A female patient aged 48 to 52. A dermoscopic image of a skin lesion: 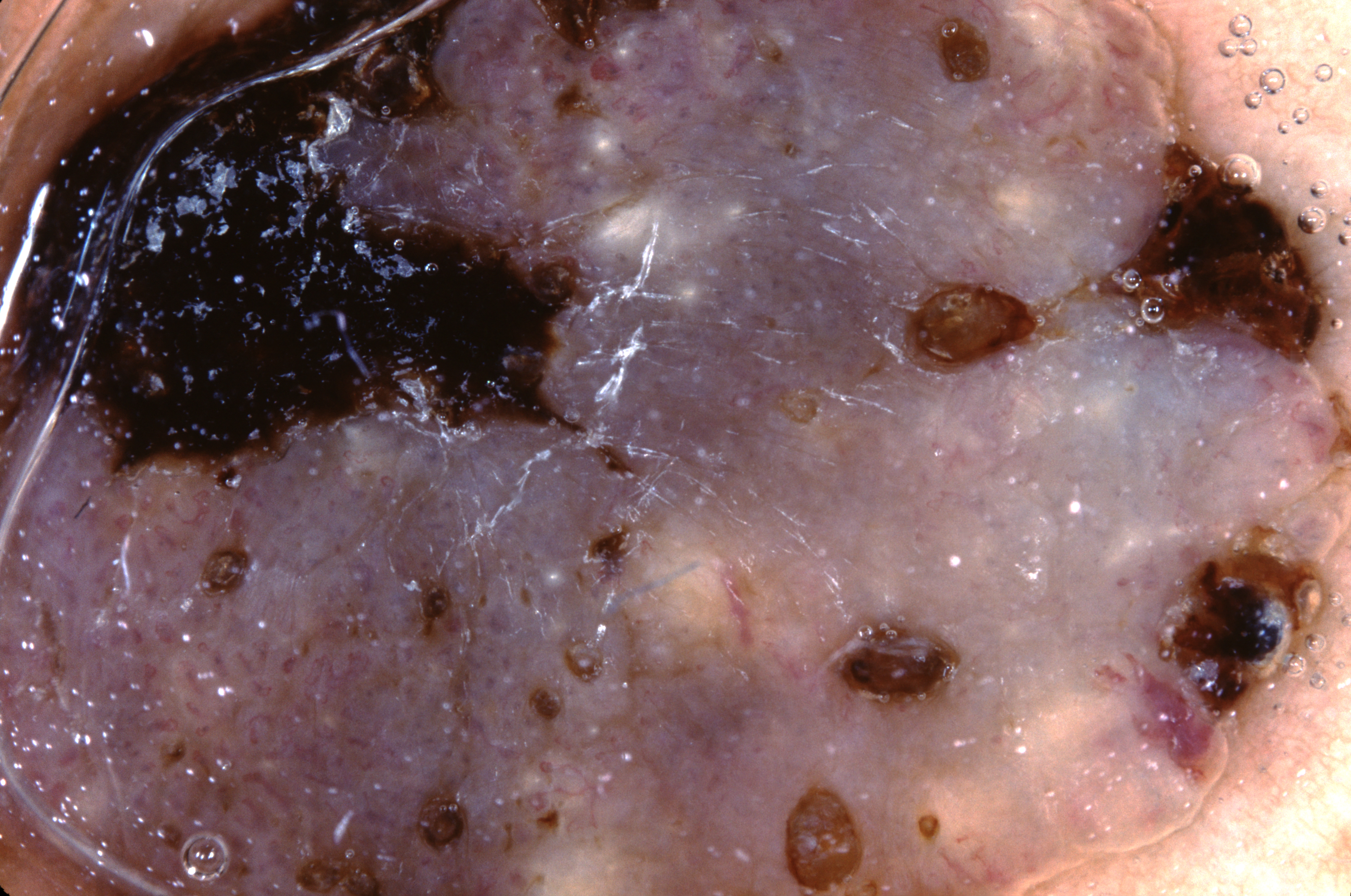{
  "lesion_location": "spans the dermoscopic field",
  "dermoscopic_features": {
    "present": [
      "milia-like cysts"
    ],
    "absent": [
      "negative network",
      "streaks",
      "pigment network"
    ]
  },
  "diagnosis": {
    "name": "seborrheic keratosis",
    "malignancy": "benign",
    "lineage": "keratinocytic",
    "provenance": "clinical"
  }
}